Per the chart, no melanoma in first-degree relatives and no previous melanoma · a dermoscopic photograph of a skin lesion · the patient is skin type III · a male subject roughly 60 years of age — 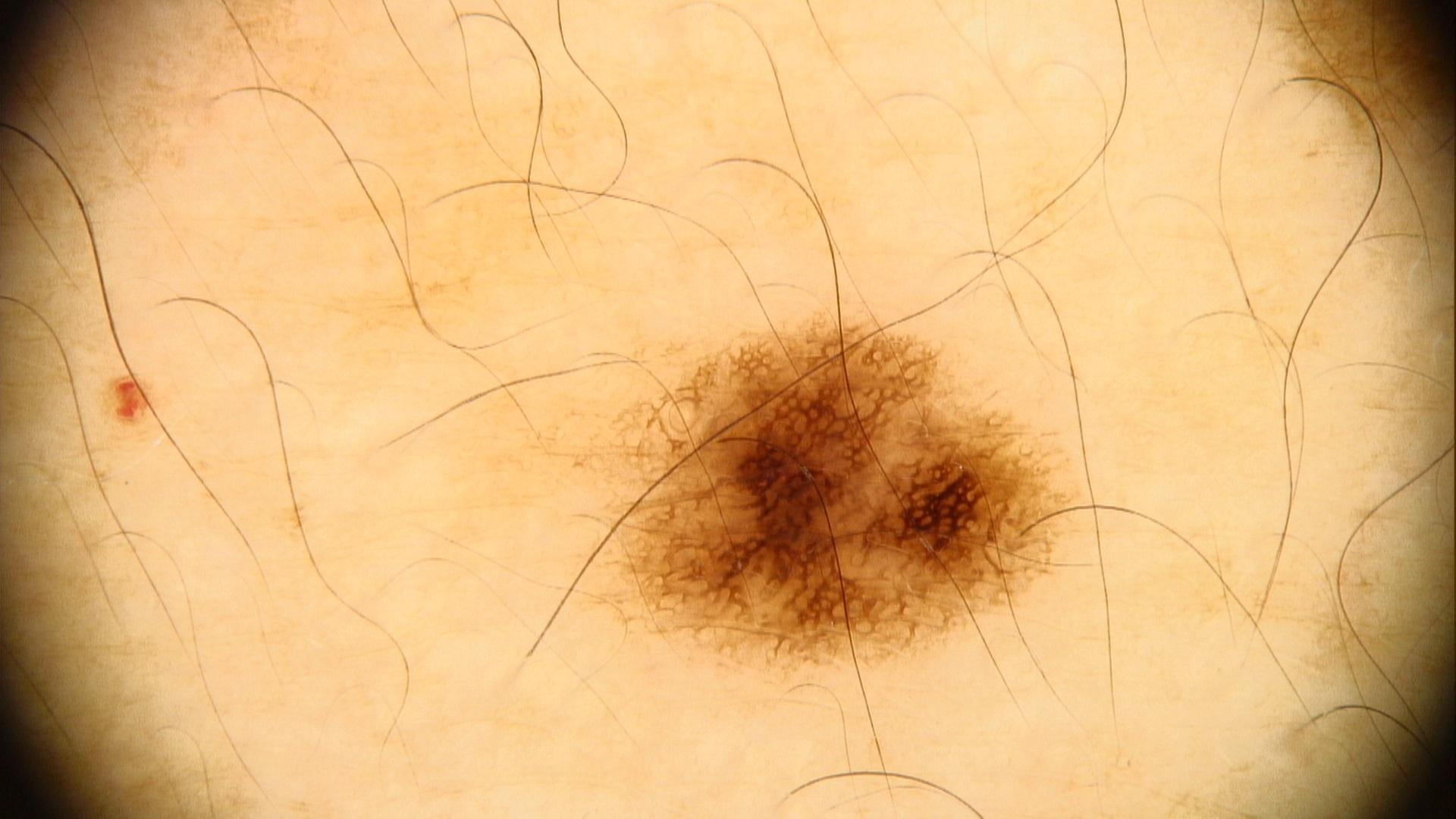Clinical context: The lesion is located on an upper extremity. Conclusion: The diagnostic impression was a nevus.